Fitzpatrick I; non-clinician graders estimated Monk skin tone scale 1 or 2 · symptoms reported: itching · the patient indicates the condition has been present for less than one week · the patient described the issue as a rash · female contributor, age 40–49 · texture is reported as raised or bumpy · the lesion involves the back of the hand, front of the torso and arm · this image was taken at an angle: 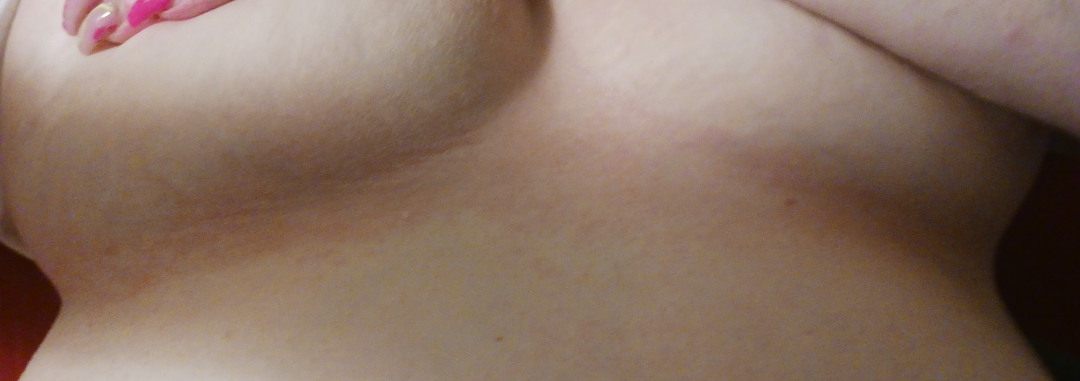Reviewed remotely by three dermatologists: in keeping with Contact dermatitis.